A close-up photograph:
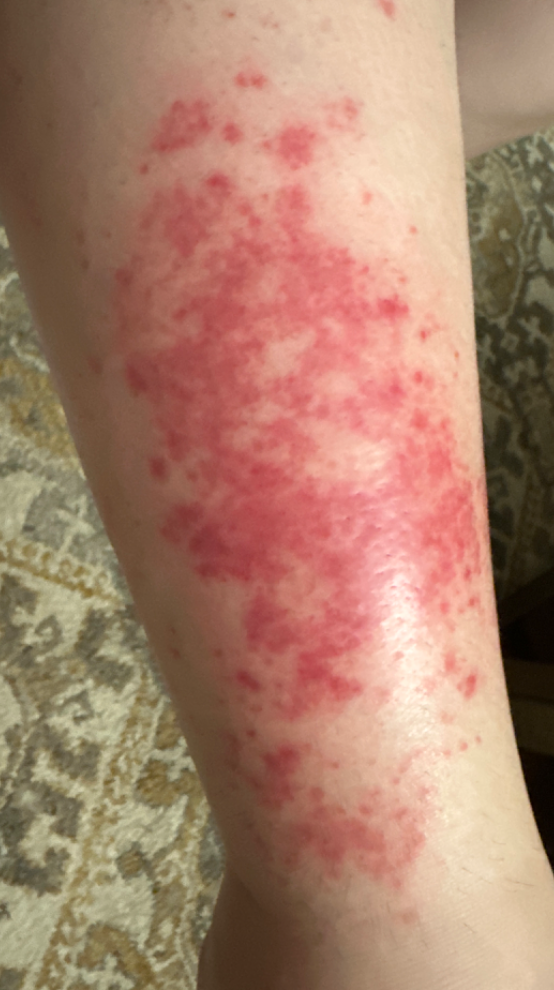Q: Could the case be diagnosed?
A: ungradable on photographic review